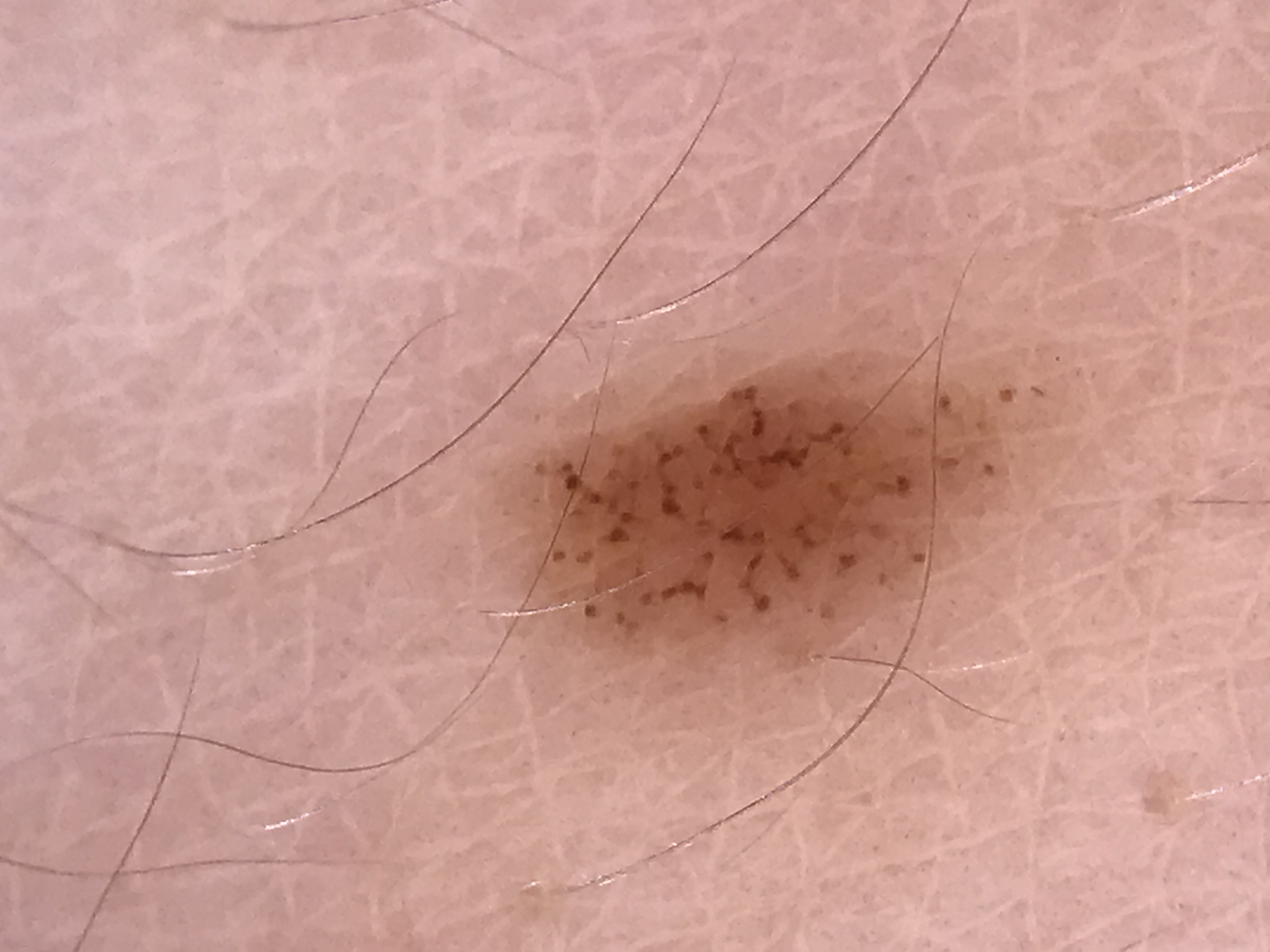image: dermoscopy; diagnostic label: junctional nevus (expert consensus).